A dermoscopic close-up of a skin lesion · a female subject, about 45 years old:
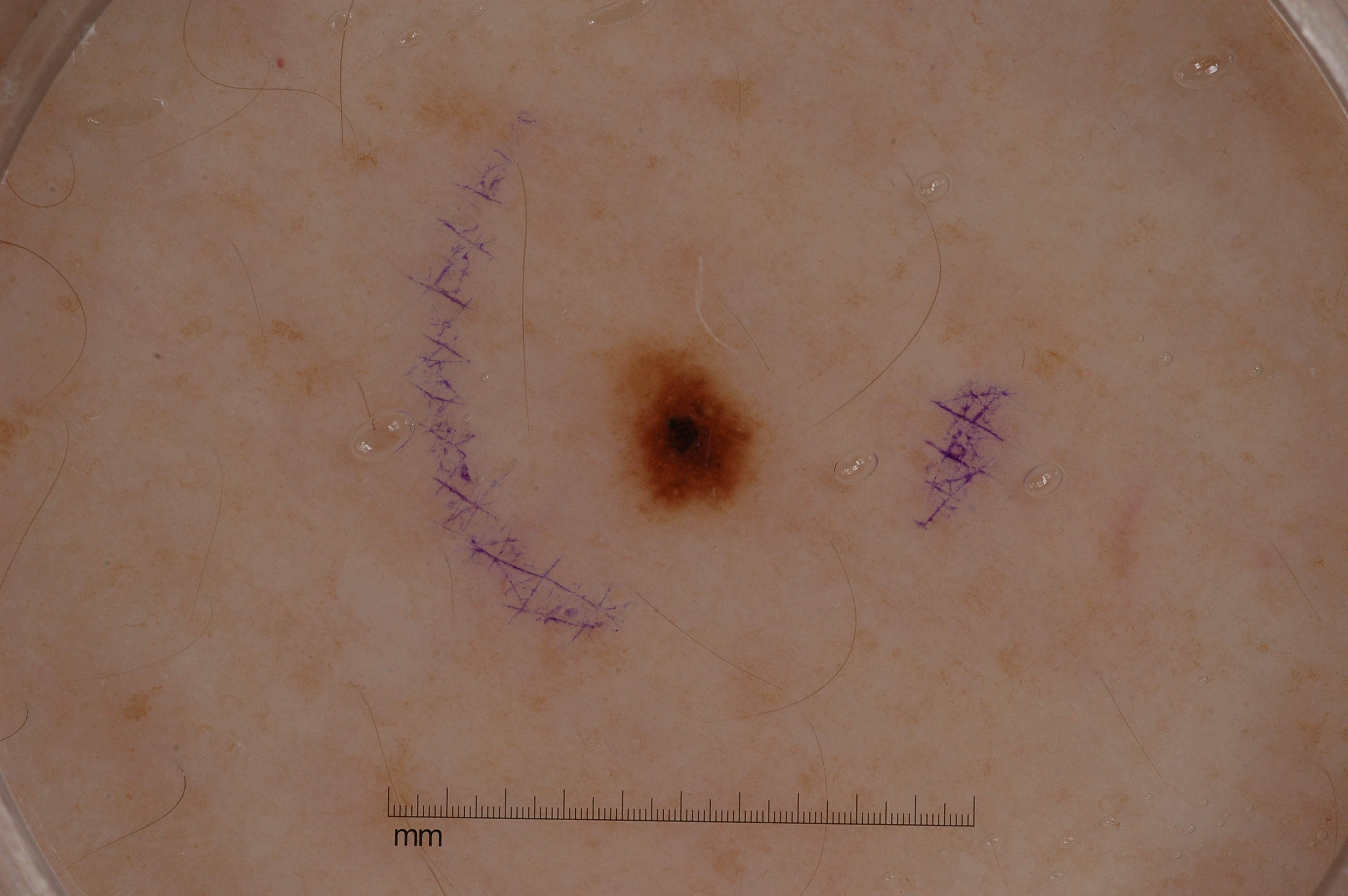{
  "dermoscopic_features": {
    "present": [],
    "absent": [
      "negative network",
      "pigment network",
      "milia-like cysts",
      "streaks"
    ]
  },
  "lesion_extent": {
    "approx_field_fraction_pct": 2
  },
  "lesion_location": {
    "bbox_xyxy": [
      611,
      336,
      758,
      518
    ]
  },
  "diagnosis": {
    "name": "melanocytic nevus",
    "malignancy": "benign",
    "lineage": "melanocytic",
    "provenance": "clinical"
  }
}